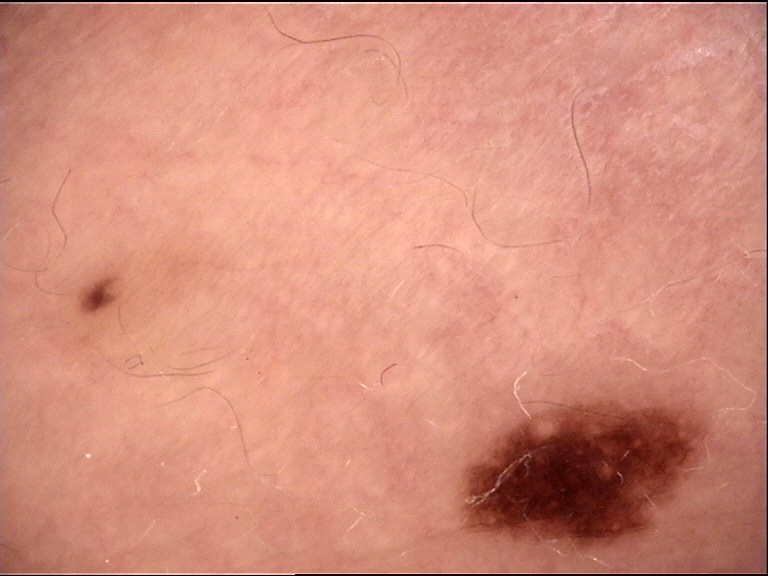imaging = dermatoscopy | class = dysplastic junctional nevus (expert consensus).